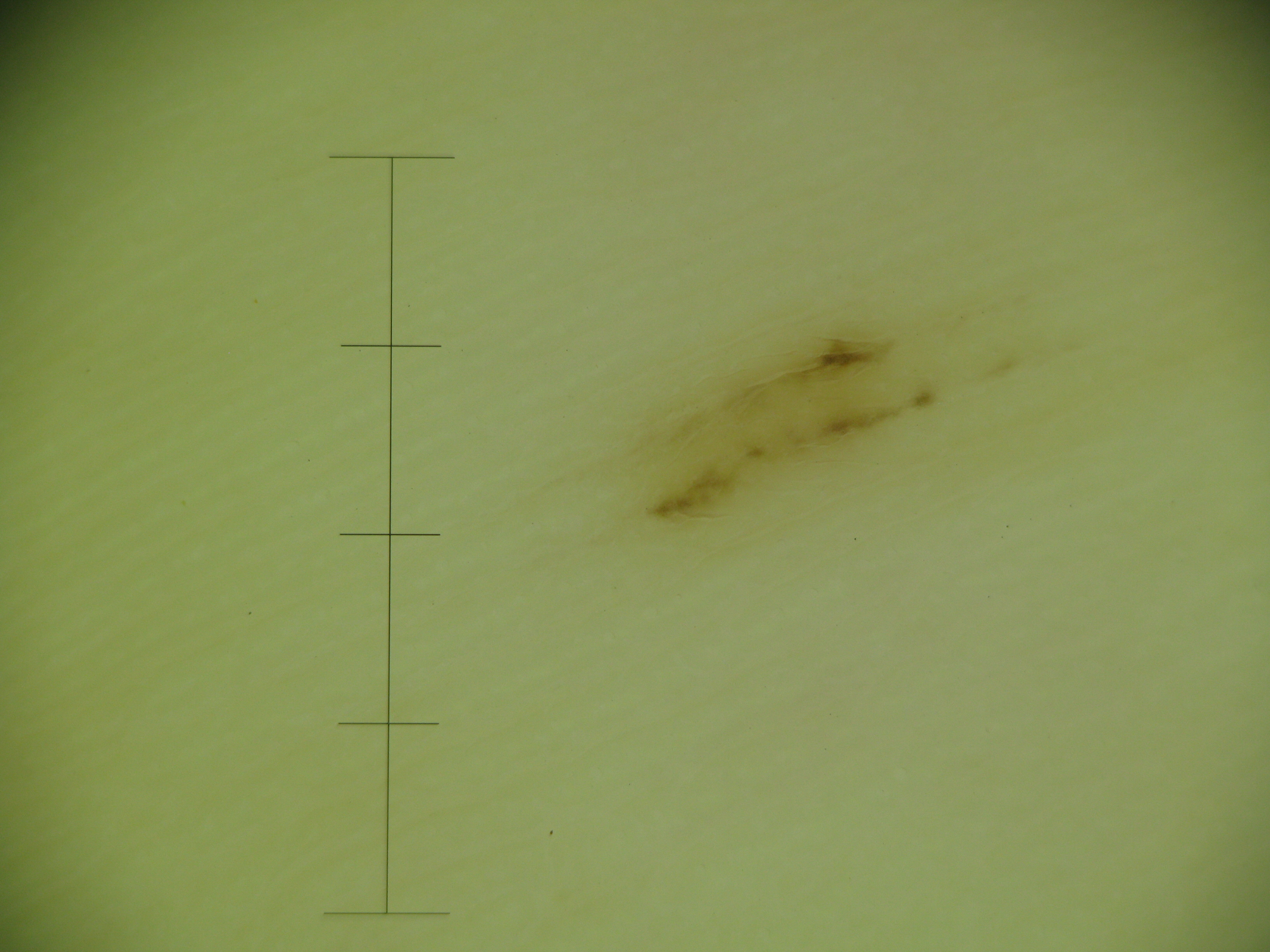Impression:
Labeled as an acral junctional nevus.